A male patient age 62; the patient says their skin reddens with sun exposure; few moles overall by the patient's own estimate; dermoscopy of a skin lesion; acquired for a research image collection, with no referral diagnosis.
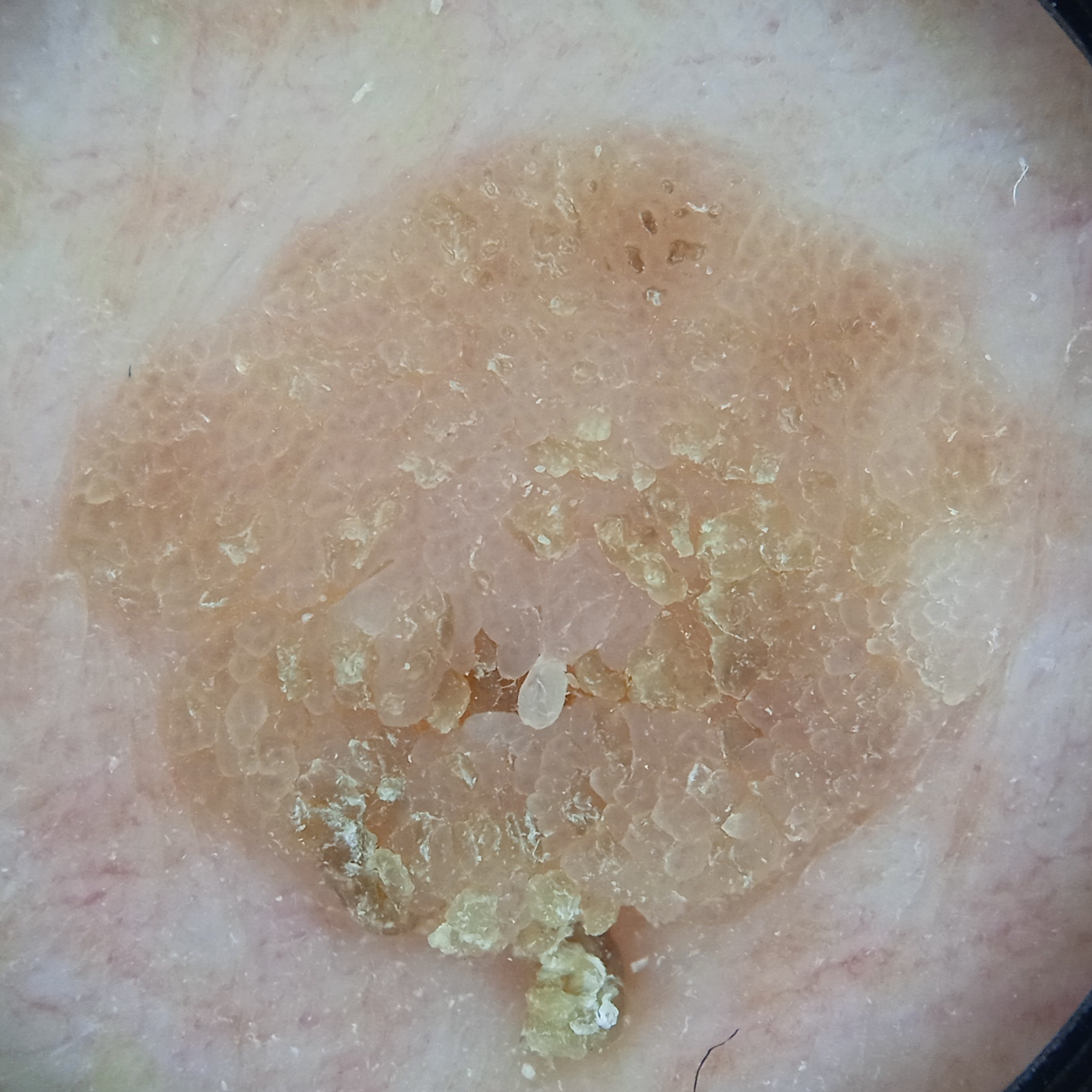location = the torso; lesion size = 11.3 mm; assessment = seborrheic keratosis (dermatologist consensus).